A dermoscopic close-up of a skin lesion. A male patient in their mid- to late 20s.
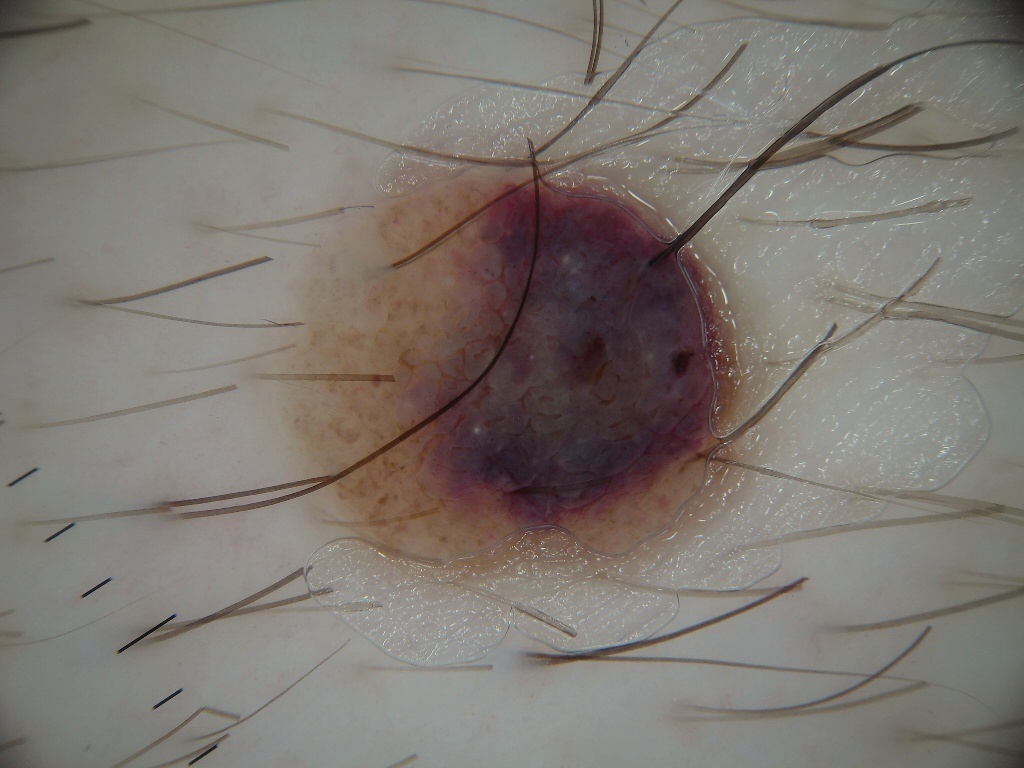dermoscopic pattern — milia-like cysts; absent: globules, negative network, streaks, and pigment network
lesion bbox — left=267, top=164, right=738, bottom=566
lesion extent — moderate
assessment — a melanocytic nevus